The photograph is a close-up of the affected area. The patient described the issue as a rash. The arm and head or neck are involved. Fitzpatrick phototype IV: 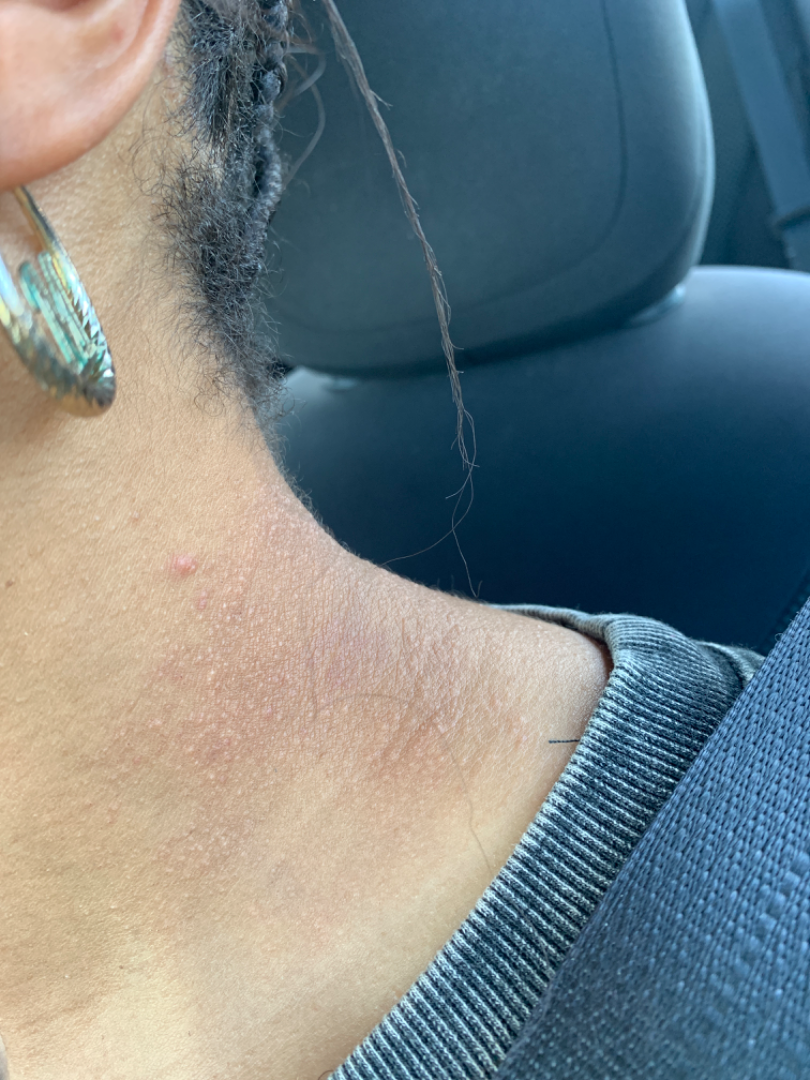differential diagnosis — single-reviewer assessment: favoring Lichen Simplex Chronicus; also raised was Acanthosis nigricans; also consider PXE (pseudoxanthoma elasticum) like syndrome